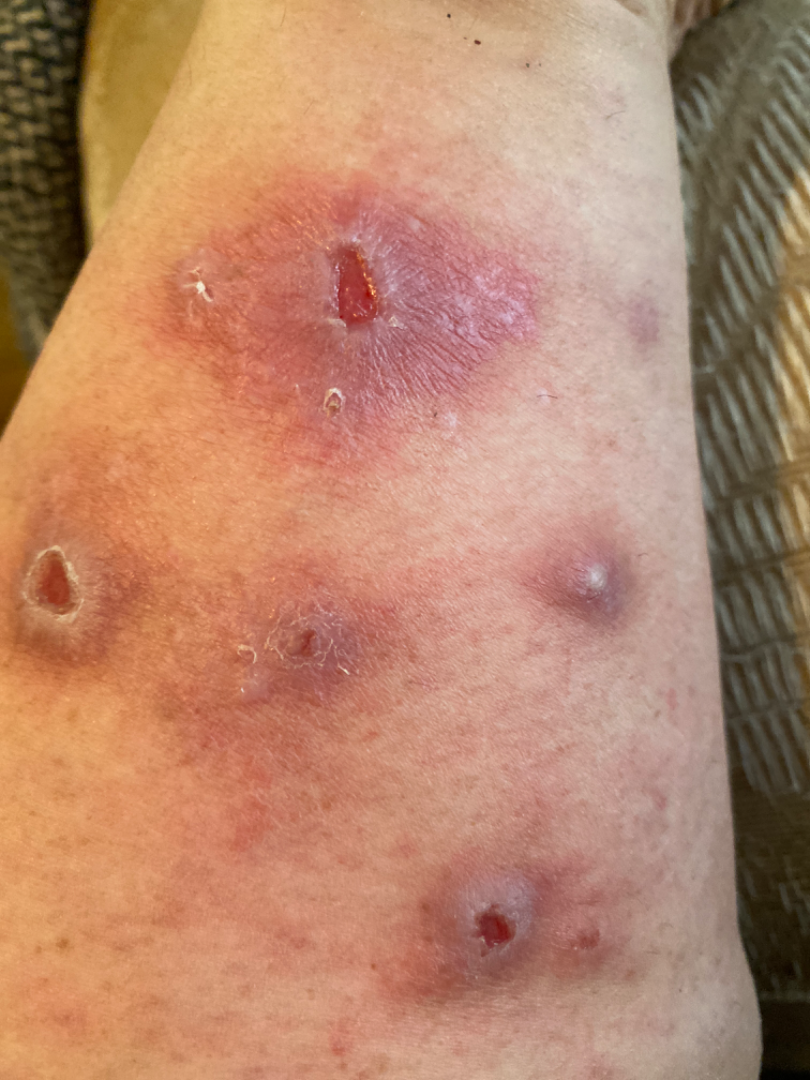The image was not sufficient for the reviewer to characterize the skin condition.